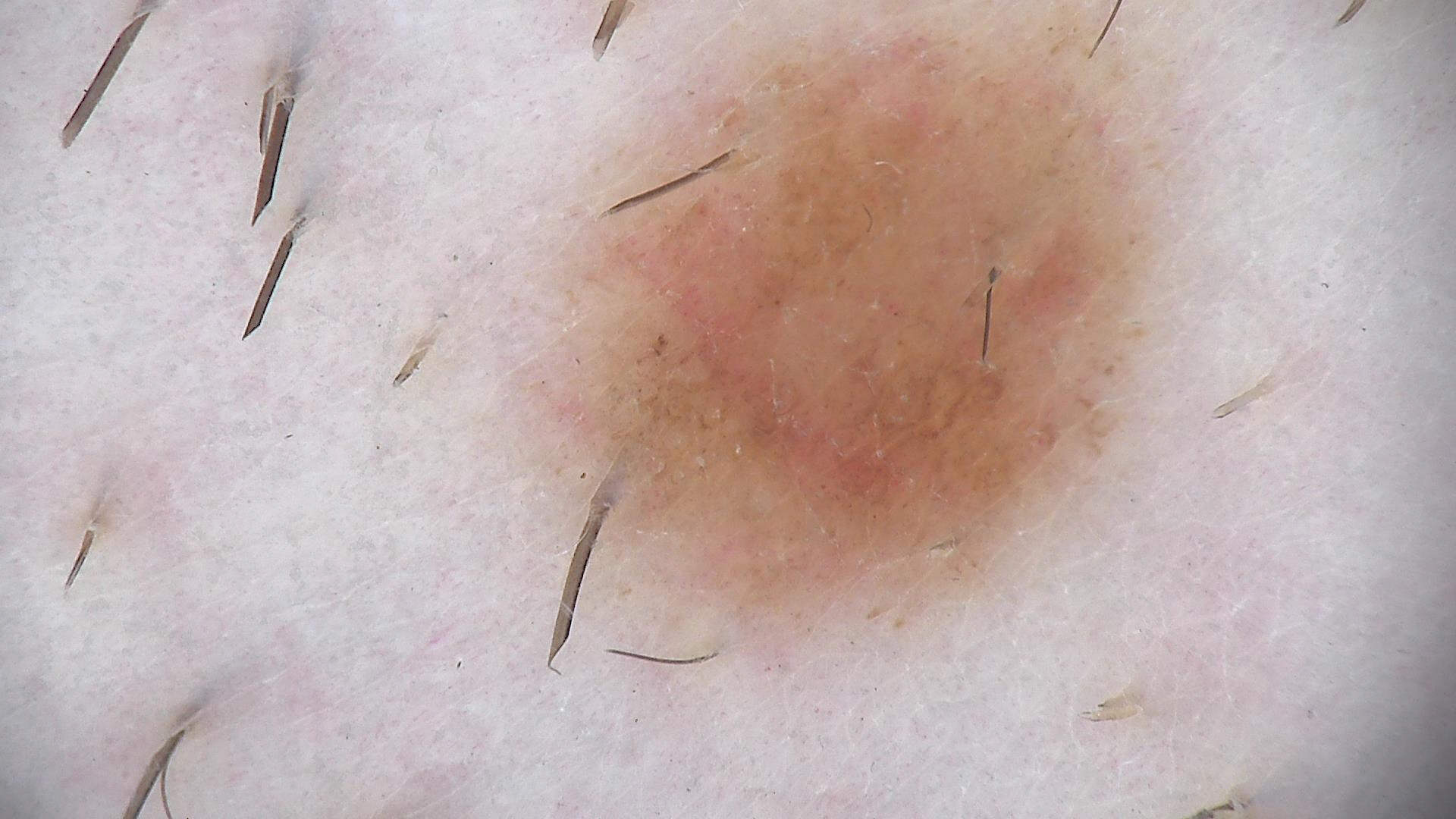Findings:
– imaging: dermoscopy
– lesion type: banal
– diagnosis: compound nevus (expert consensus)